The contributor is 30–39, female · the affected area is the head or neck · an image taken at a distance — 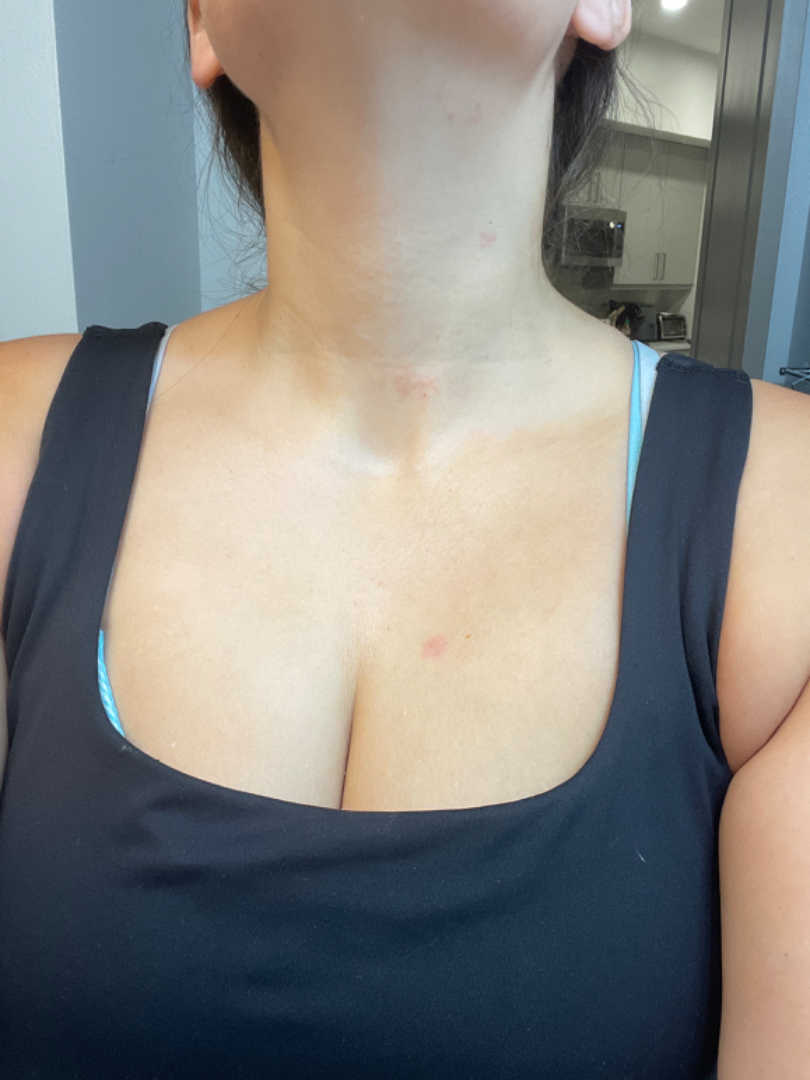assessment: Eczema (most likely); Allergic Contact Dermatitis (possible); Tinea (possible); Contact dermatitis (unlikely).